This image was taken at a distance:
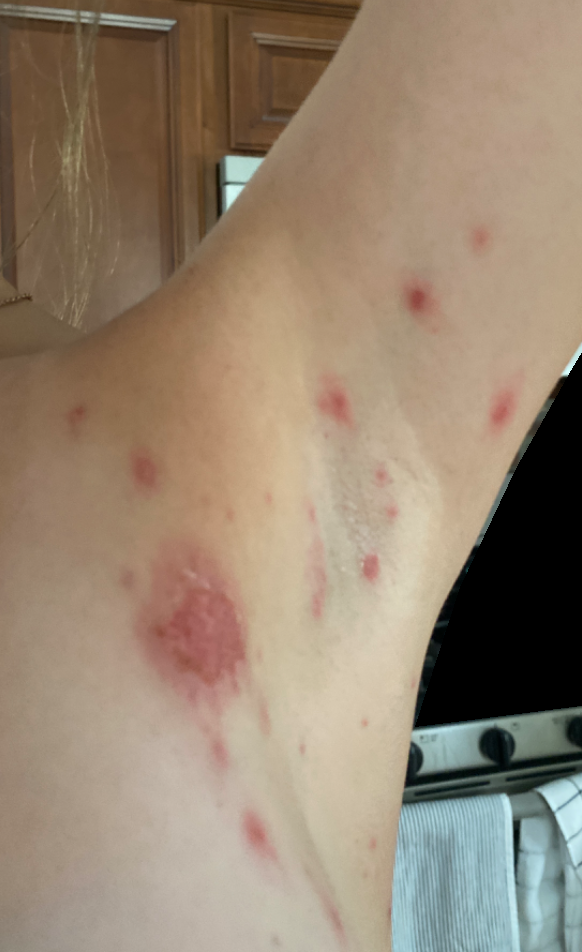clinical impression — the leading consideration is Impetigo; the differential also includes Folliculitis.